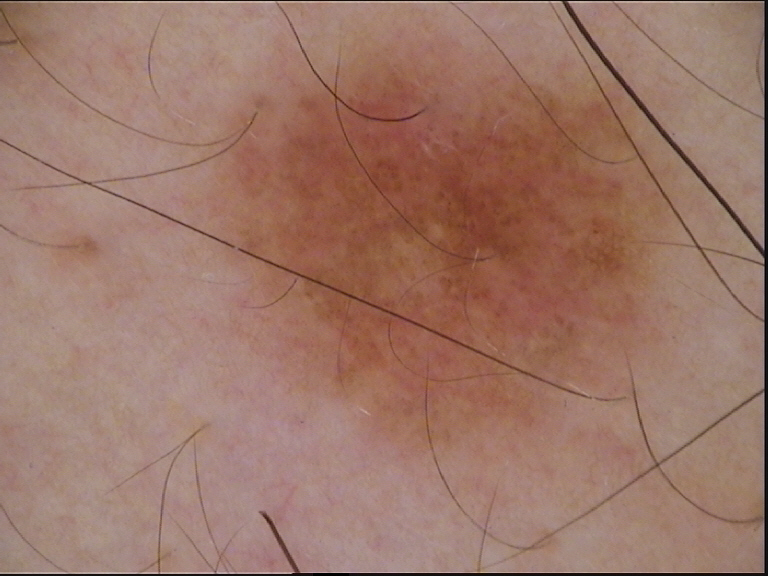Findings:
– modality: dermoscopy
– diagnosis: dysplastic junctional nevus (expert consensus)